The affected area is the leg. The contributor is a female aged 18–29. The patient indicates bothersome appearance and darkening. The patient indicates the lesion is flat. Reported duration is one to three months. Associated systemic symptoms include fatigue. An image taken at an angle — 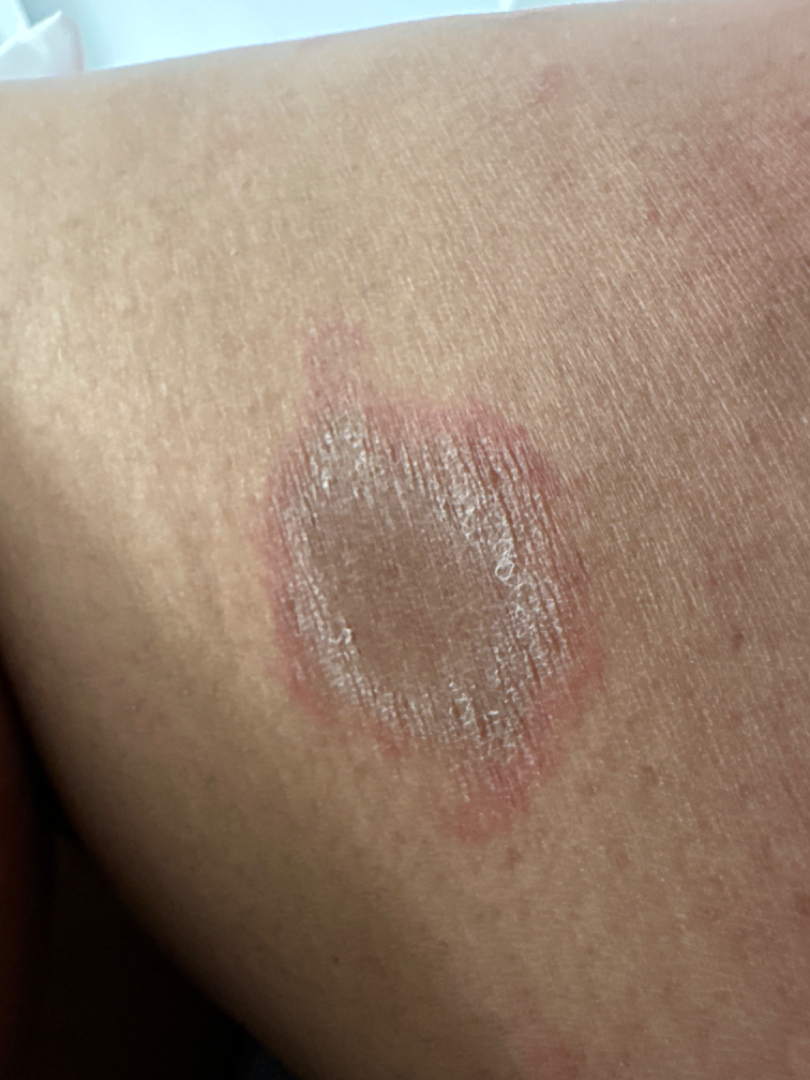- impression · most consistent with Drug Rash